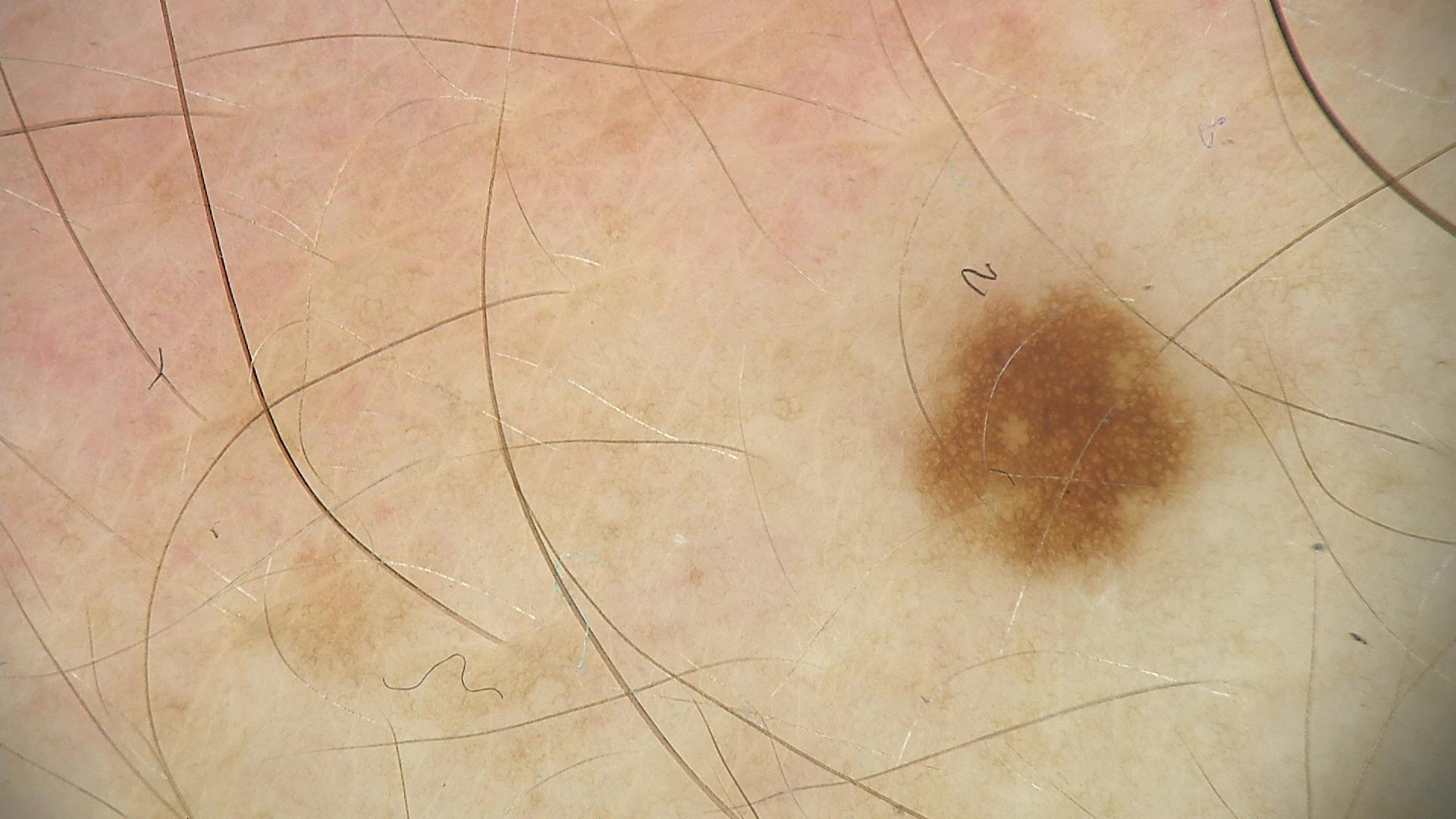image: dermoscopy
diagnosis:
  name: dysplastic junctional nevus
  code: jd
  malignancy: benign
  super_class: melanocytic
  confirmation: expert consensus